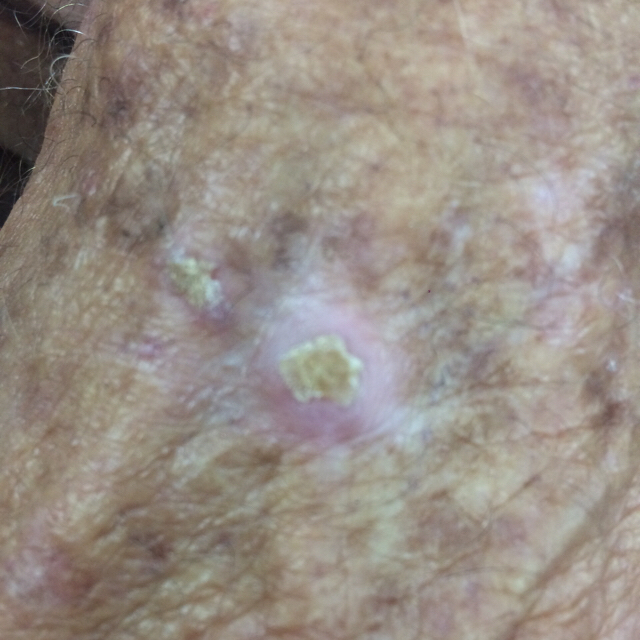Case:
* modality · smartphone clinical photo
* patient · male, 69 years old
* site · a hand
* patient-reported symptoms · itching, elevation / no growth
* diagnosis · actinic keratosis (biopsy-proven)